A dermoscopic photograph of a skin lesion.
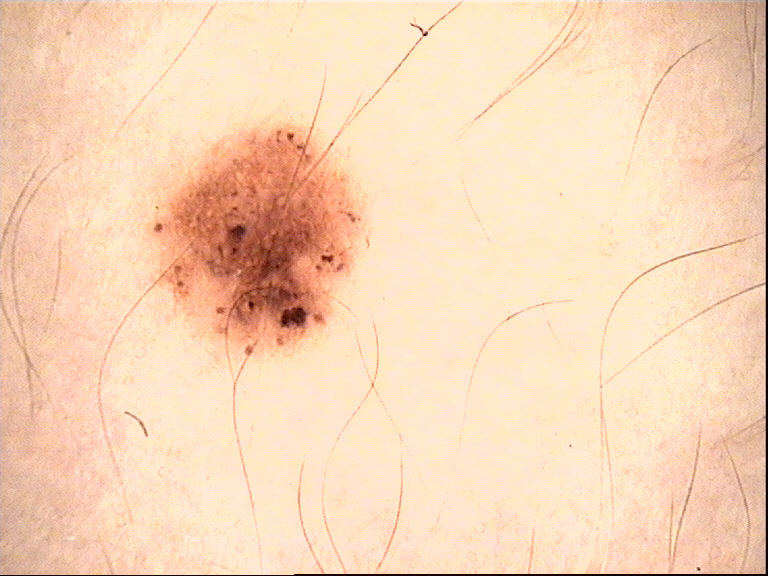Q: What was the diagnostic impression?
A: dysplastic junctional nevus (expert consensus)